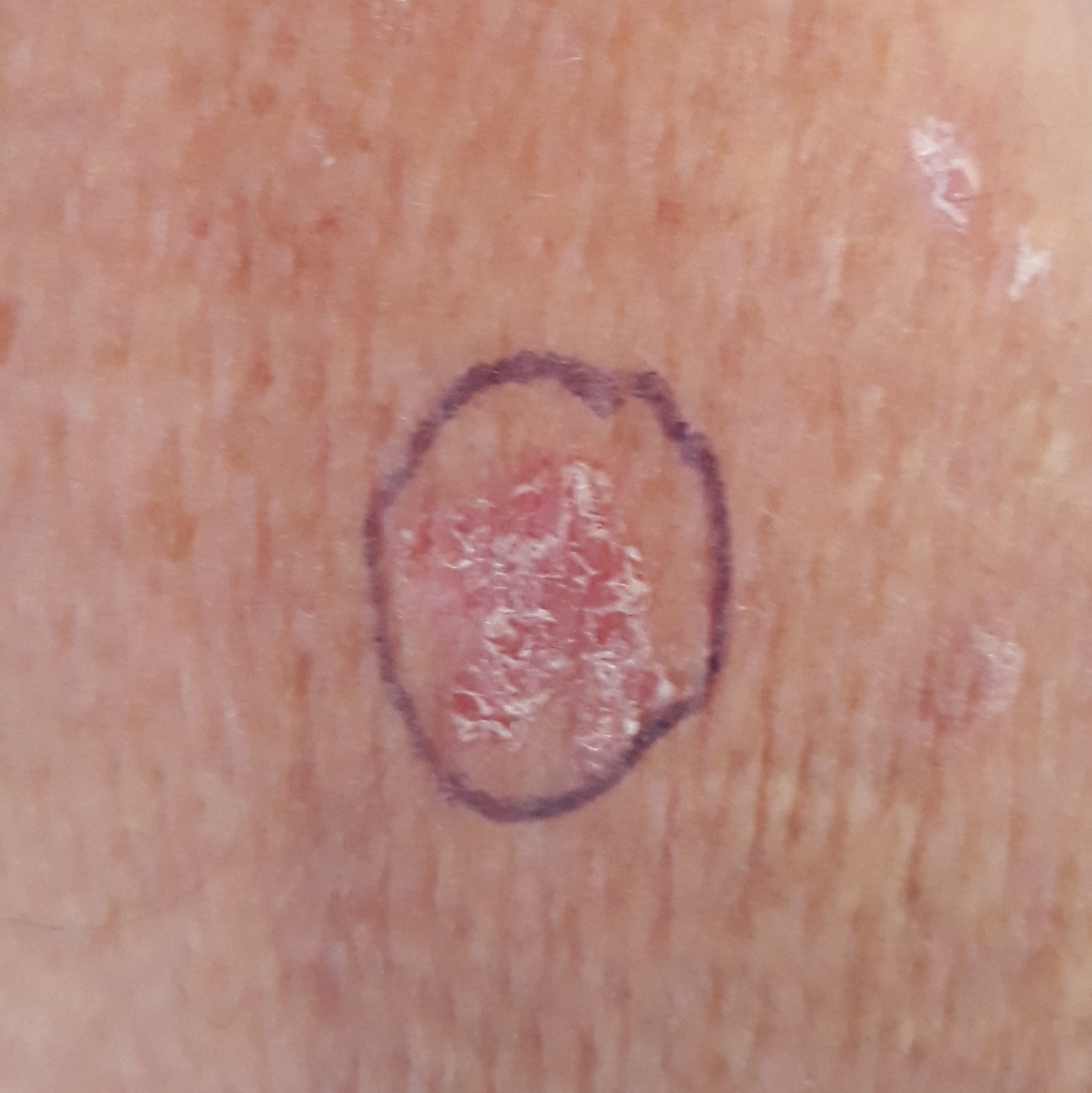patient: in their mid-60s; modality: clinical photo; symptoms: itching; impression: actinic keratosis (clinical consensus).